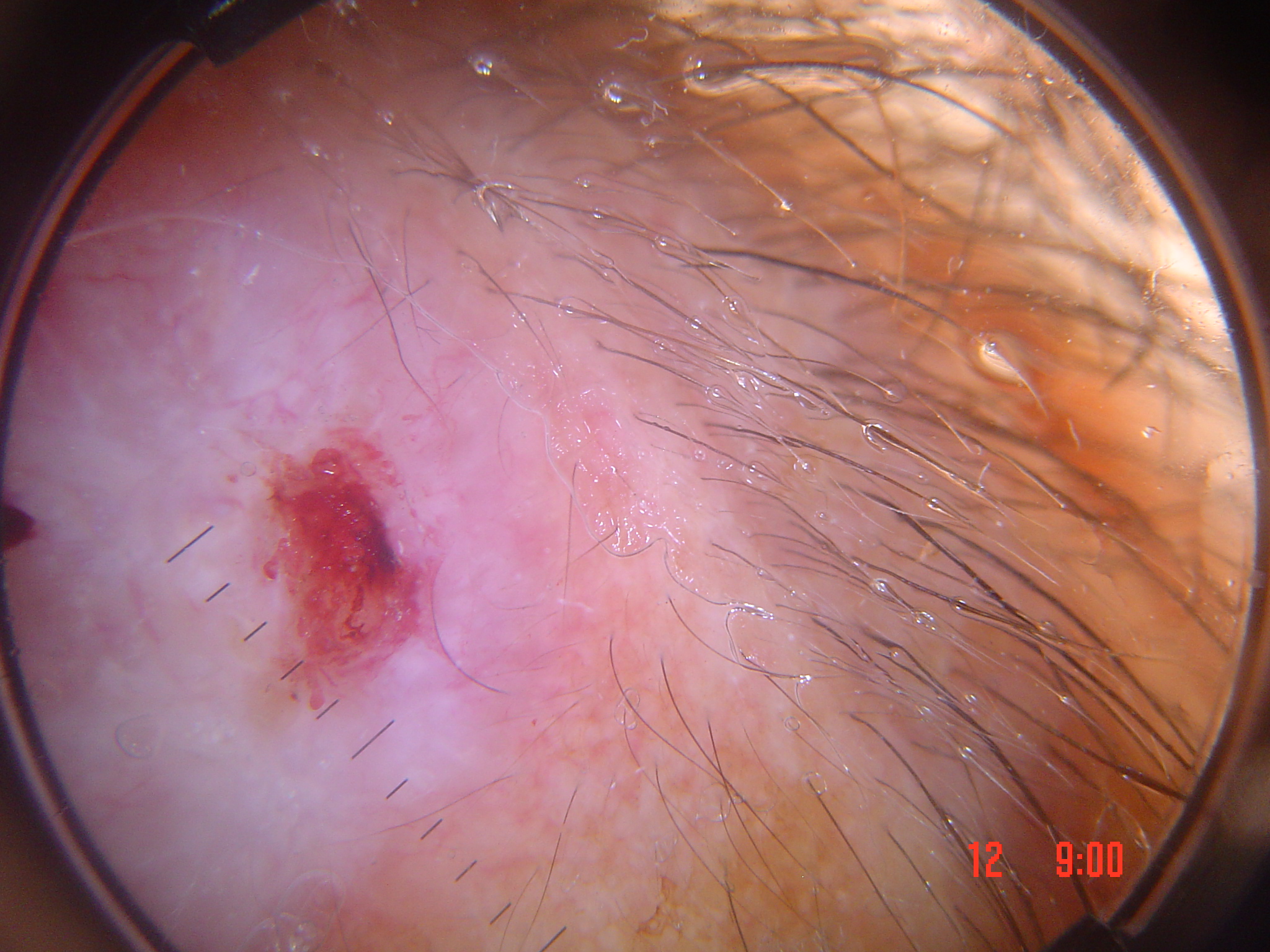Conclusion:
The biopsy diagnosis was a keratinocytic lesion — a basal cell carcinoma.